A dermoscopic view of a skin lesion.
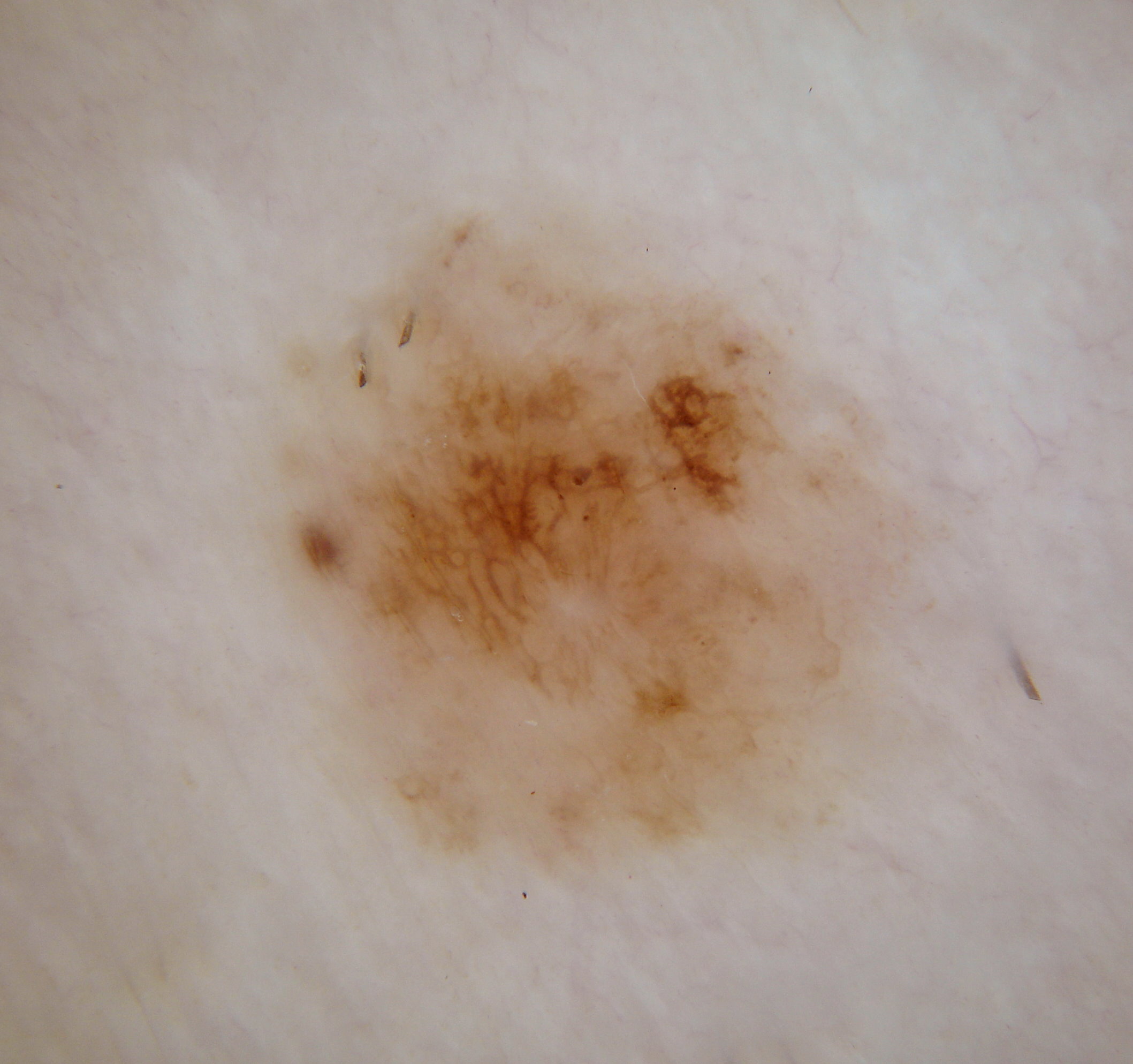As (left, top, right, bottom), the visible lesion spans <bbox>246, 213, 948, 893</bbox>. The lesion takes up a moderate portion of the field. Dermoscopic assessment notes globules and pigment network. The diagnostic assessment was a melanocytic nevus.